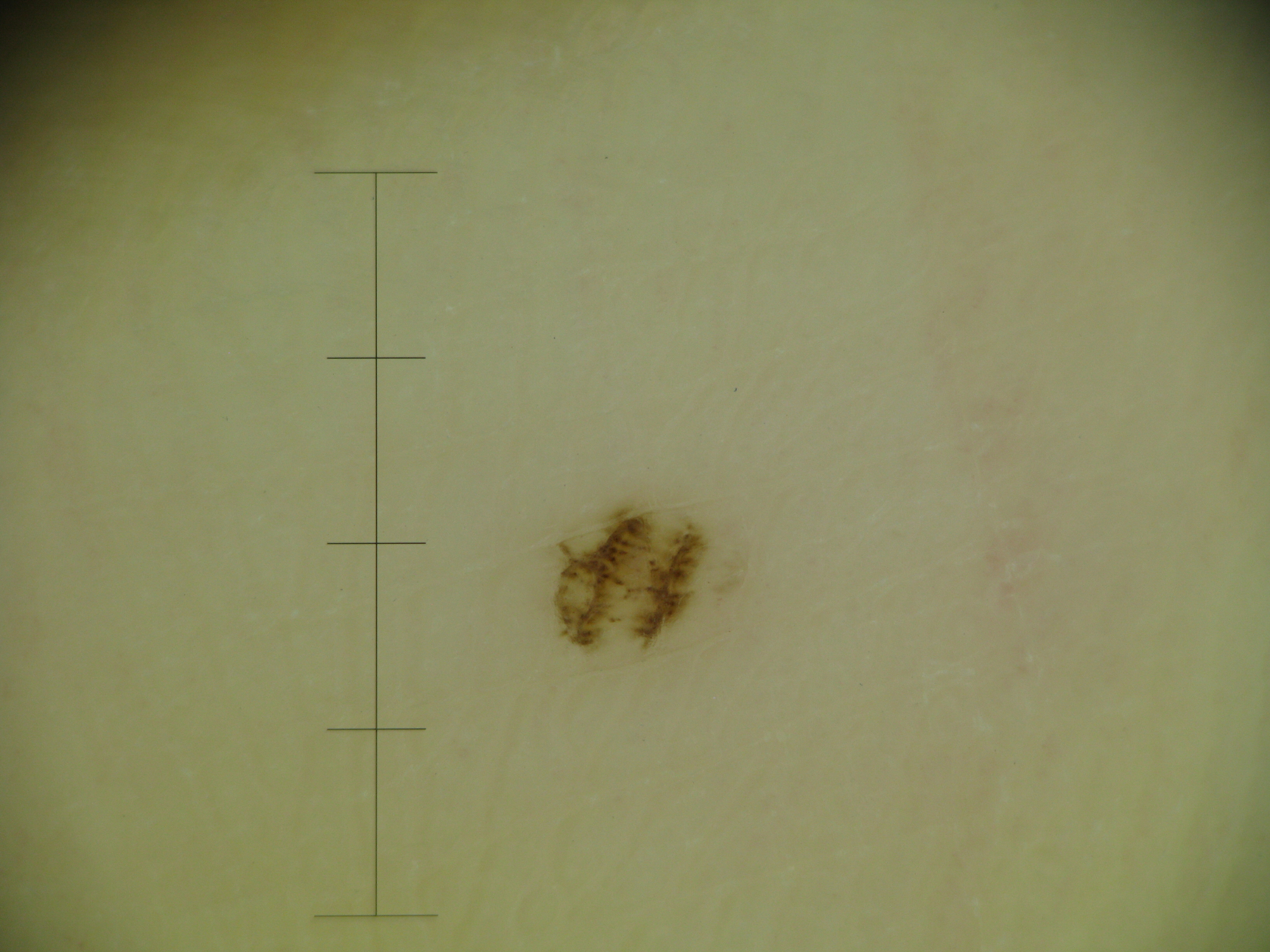Labeled as a banal lesion — an acral junctional nevus.